Close-up view — 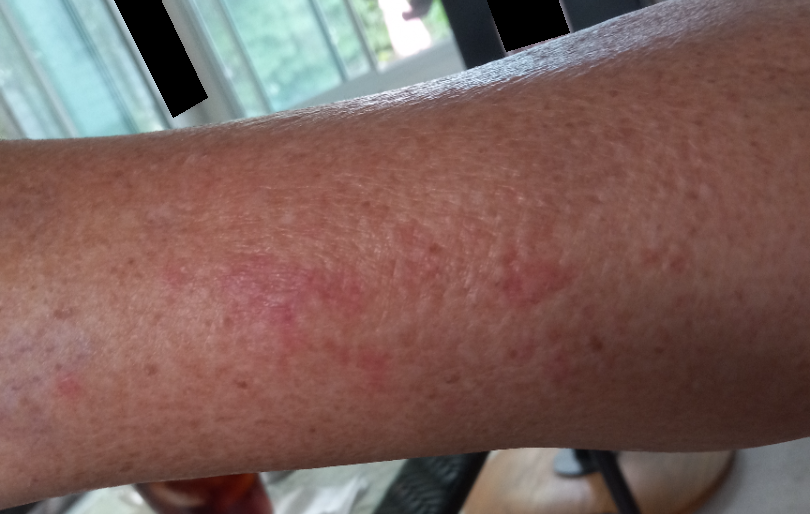Findings:
The skin findings could not be characterized from the image.